The patient is a male aged around 50. A dermoscopic view of a skin lesion:
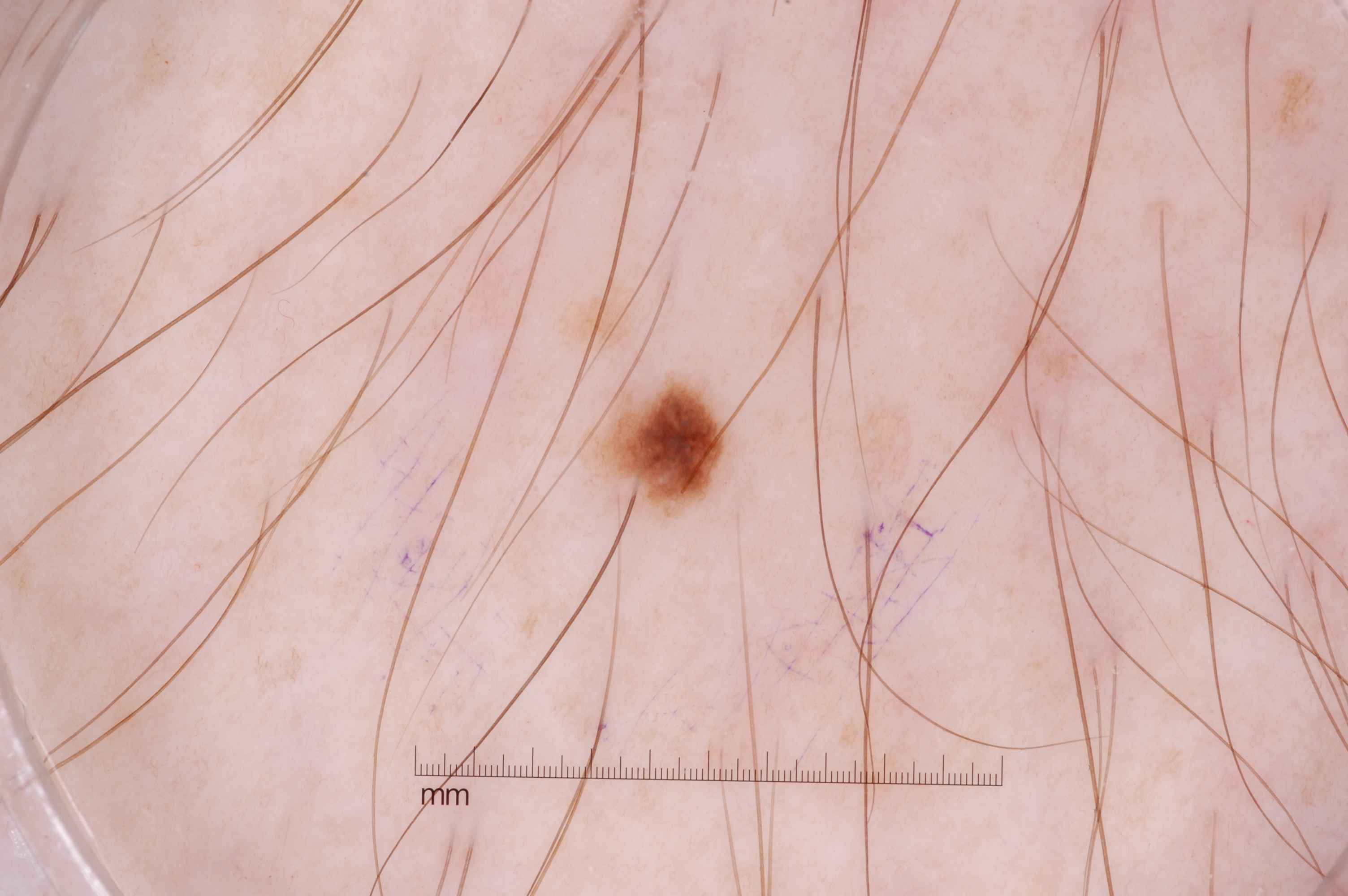| field | value |
|---|---|
| features | pigment network; absent: streaks, milia-like cysts, and negative network |
| bounding box | x1=574, y1=364, x2=731, y2=527 |
| extent | ~2% of the field |
| diagnosis | a melanocytic nevus, a benign skin lesion |